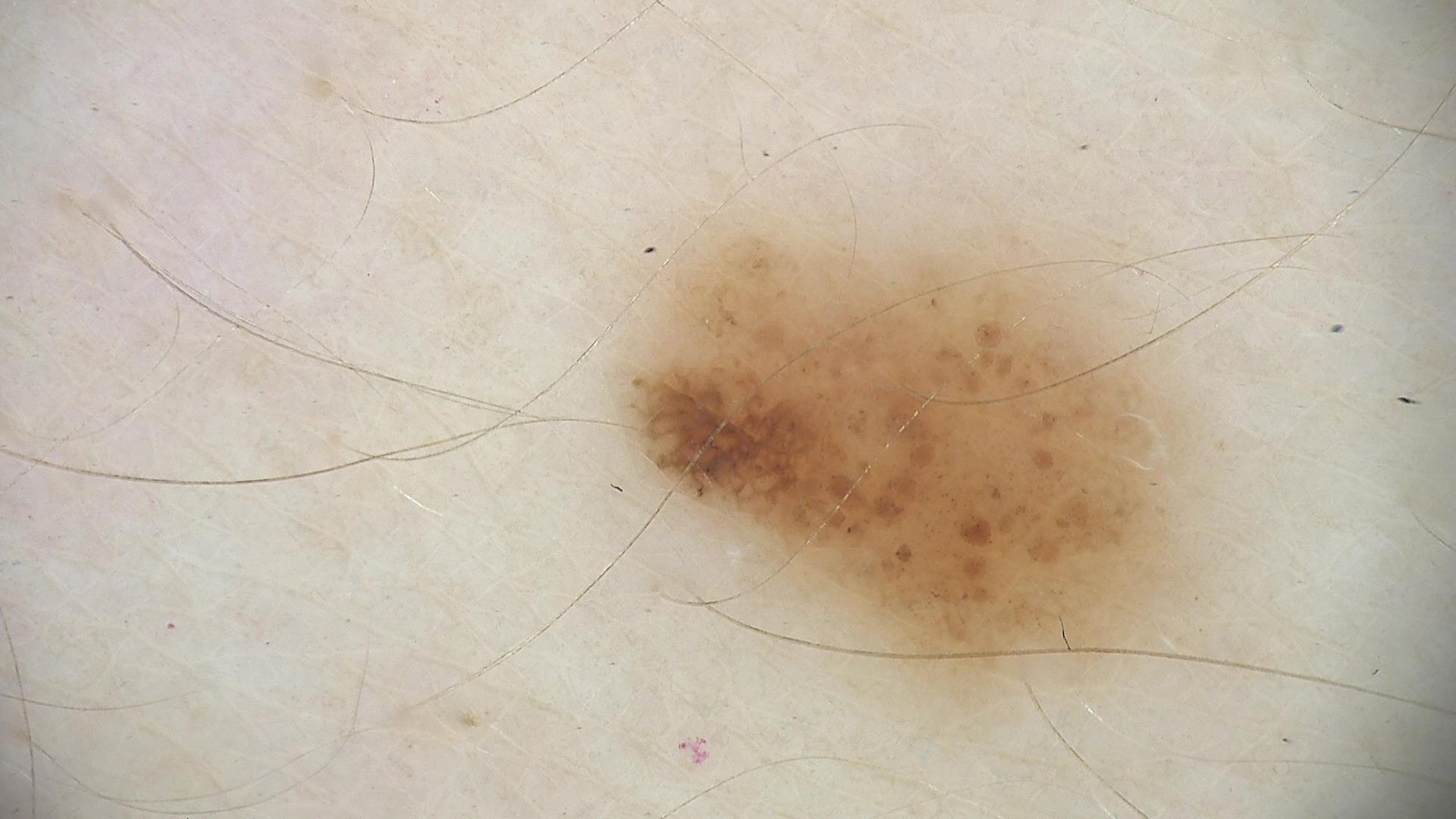imaging: dermatoscopy | label: dysplastic junctional nevus (expert consensus).